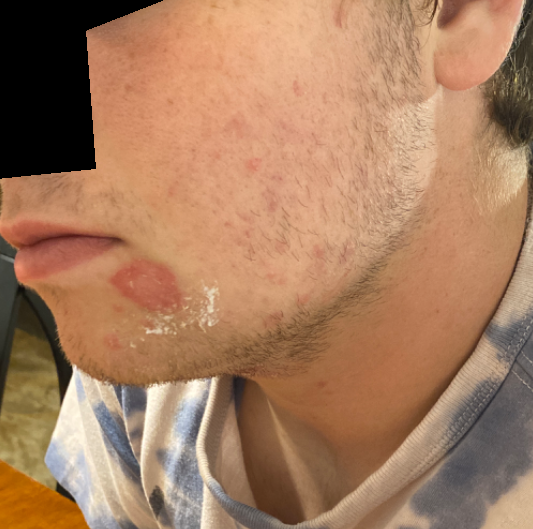The patient is 18–29, male. This image was taken at a distance. The head or neck is involved. Impetigo, Allergic Contact Dermatitis and Irritant Contact Dermatitis were considered with similar weight.